The photo was captured at a distance — 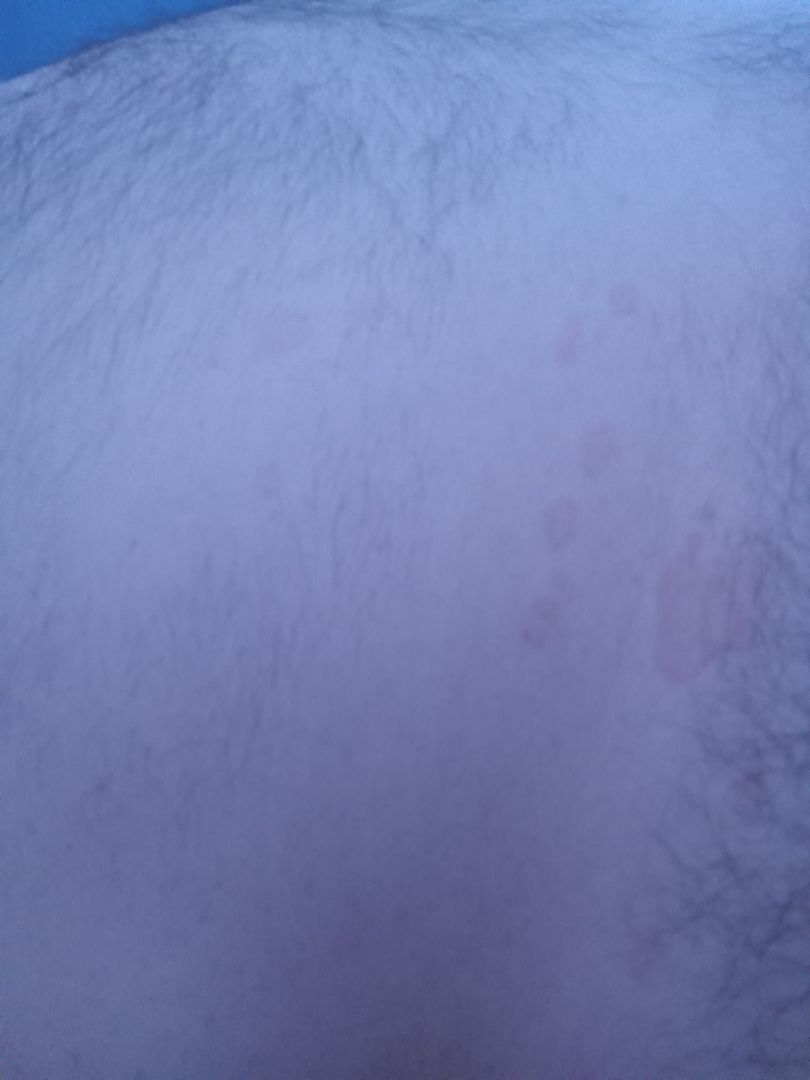assessment — indeterminate from the photograph.